A skin lesion imaged with a dermatoscope.
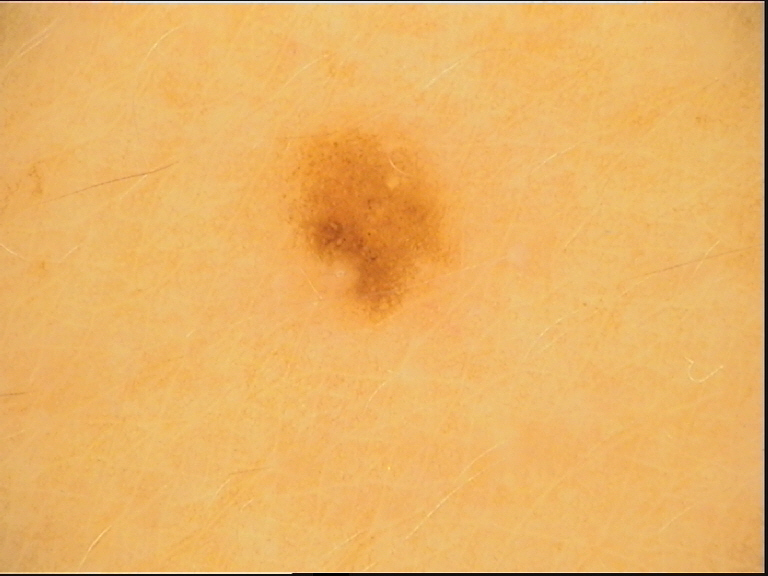class=junctional nevus (expert consensus).